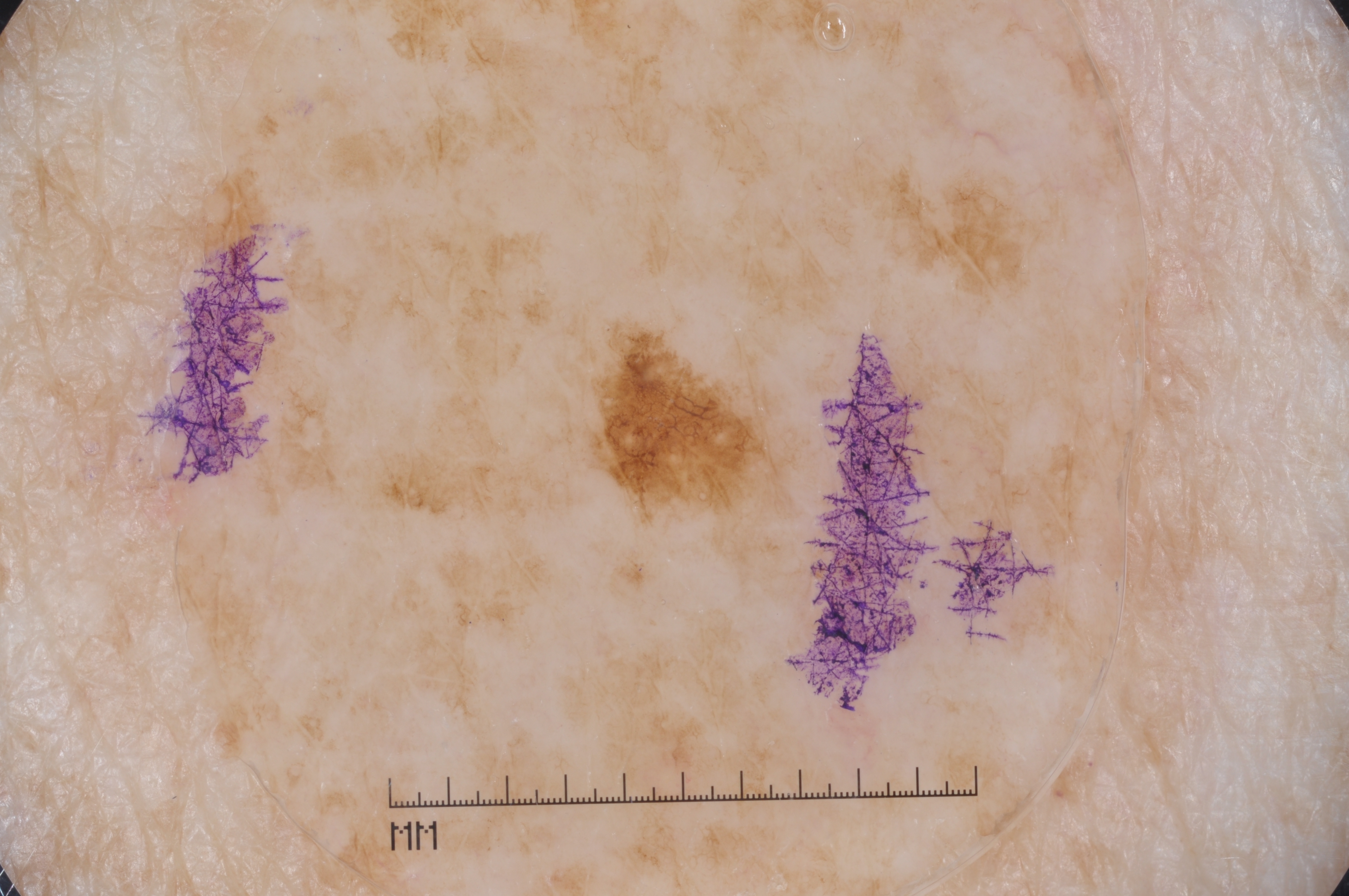A dermoscopic close-up of a skin lesion.
The patient is a male in their mid-80s or older.
As (left, top, right, bottom), the lesion occupies the region bbox=[601, 350, 780, 504].
Dermoscopically, the lesion shows pigment network, with no negative network, streaks, or milia-like cysts.
Confirmed on histopathology as a melanoma.